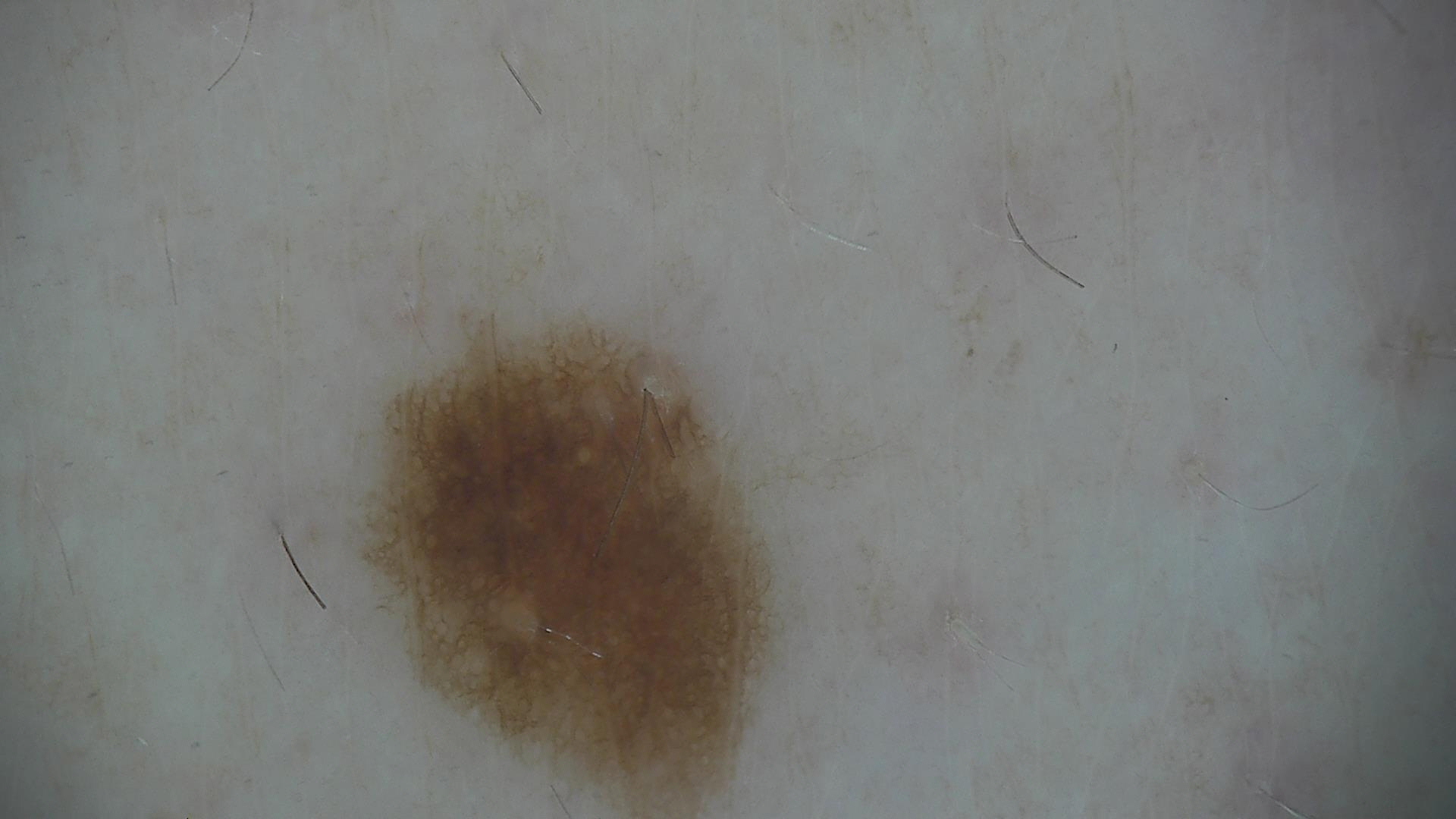Case:
– imaging · dermoscopy
– diagnostic label · dysplastic junctional nevus (expert consensus)